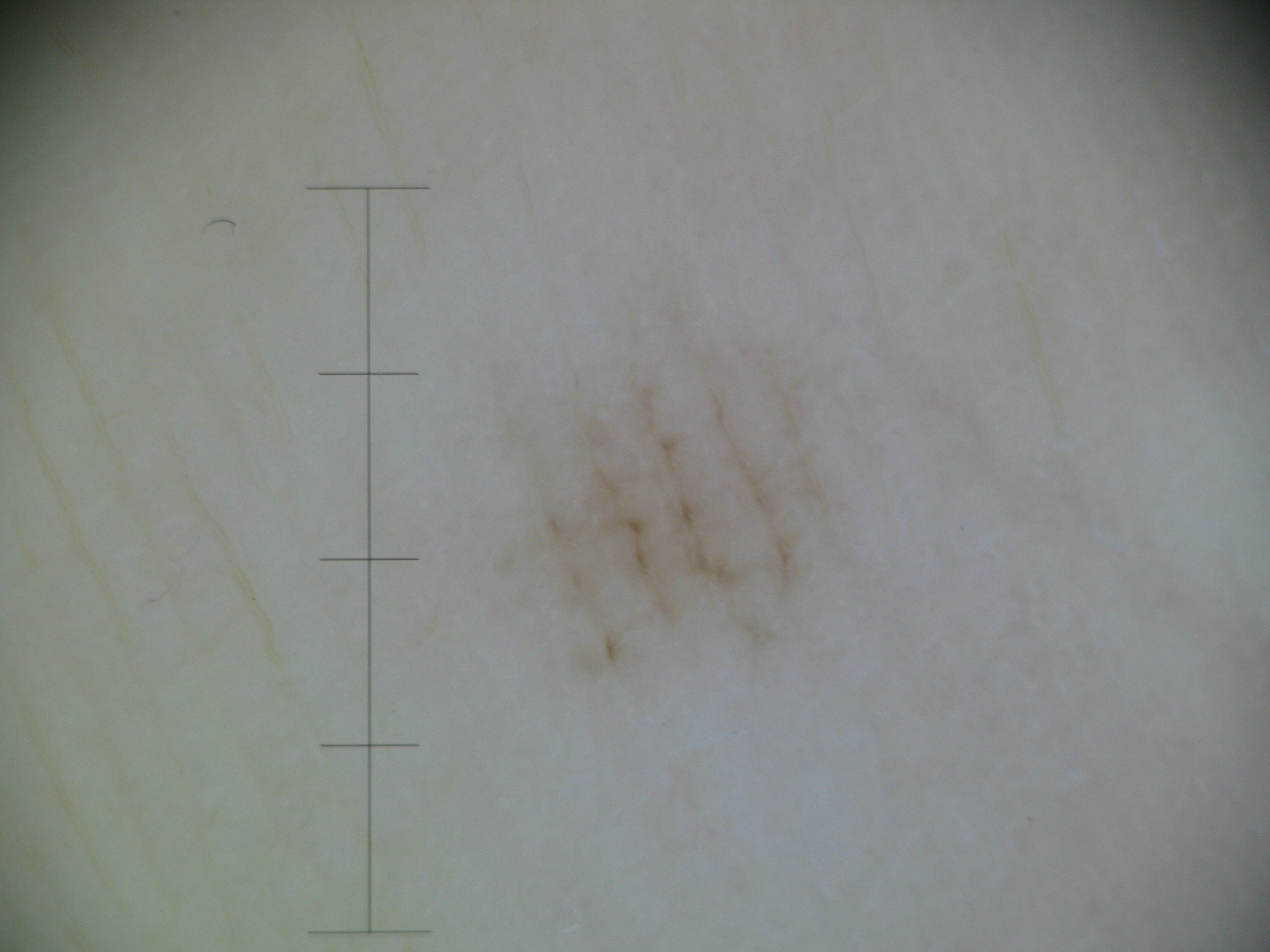A dermoscopic image of a skin lesion. This is a banal lesion. Diagnosed as an acral junctional nevus.